History notes prior malignancy (patient or family) and prior skin cancer (patient or family) · recorded as FST III · a male patient in their 70s — 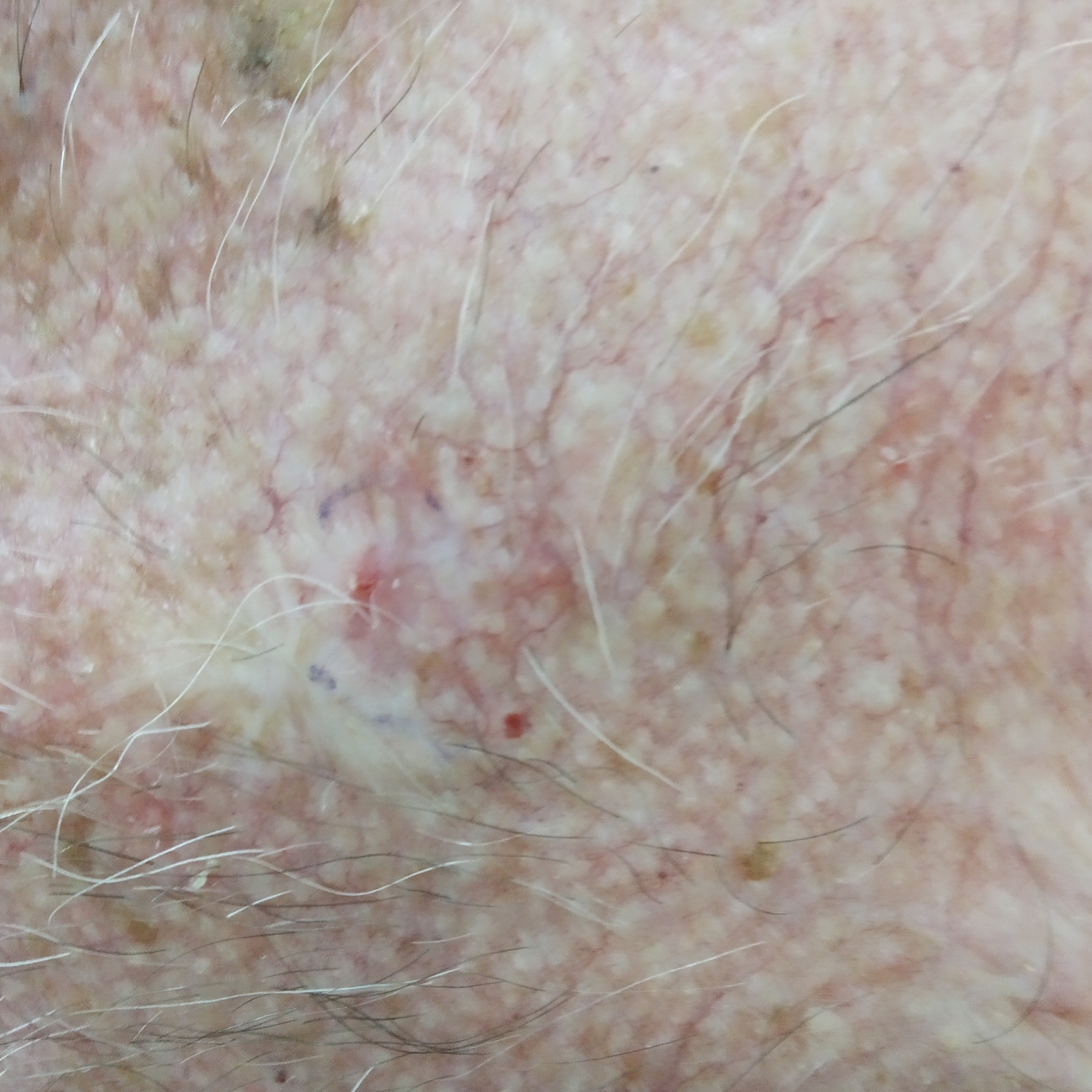The lesion was found on the chest.
The lesion measures 12 × 6 mm.
The patient describes that the lesion is not elevated and has not bled.
On biopsy, the diagnosis was an actinic keratosis.